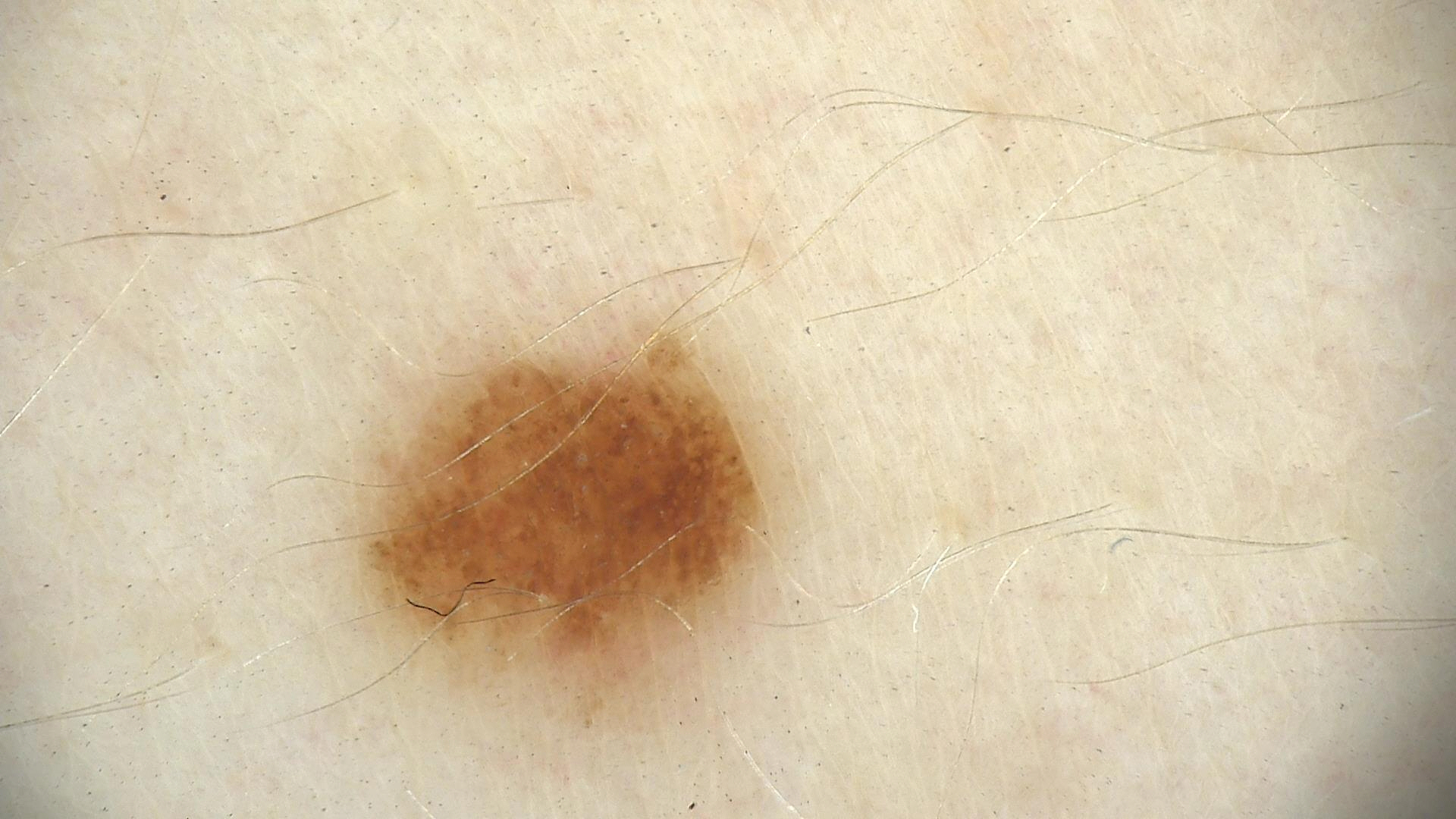<case>
<image>dermatoscopy</image>
<diagnosis>
<name>dysplastic junctional nevus</name>
<code>jd</code>
<malignancy>benign</malignancy>
<super_class>melanocytic</super_class>
<confirmation>expert consensus</confirmation>
</diagnosis>
</case>